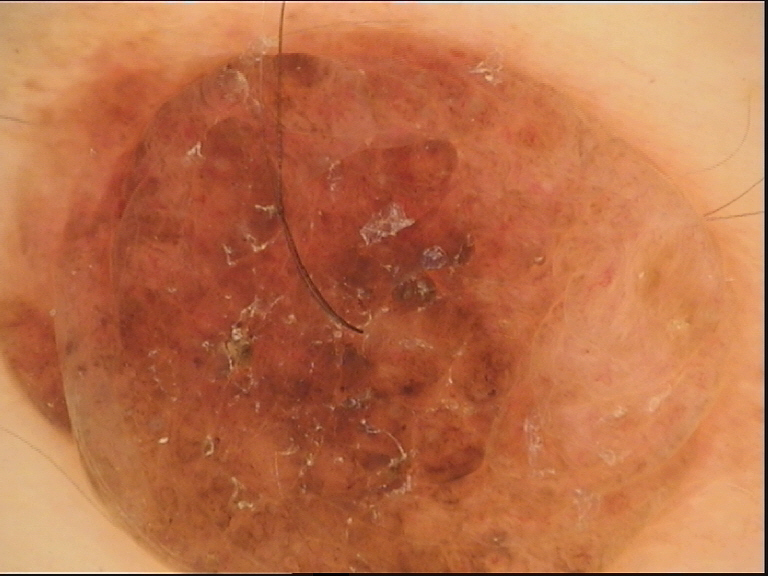image = dermoscopy; label = dermal nevus (expert consensus).